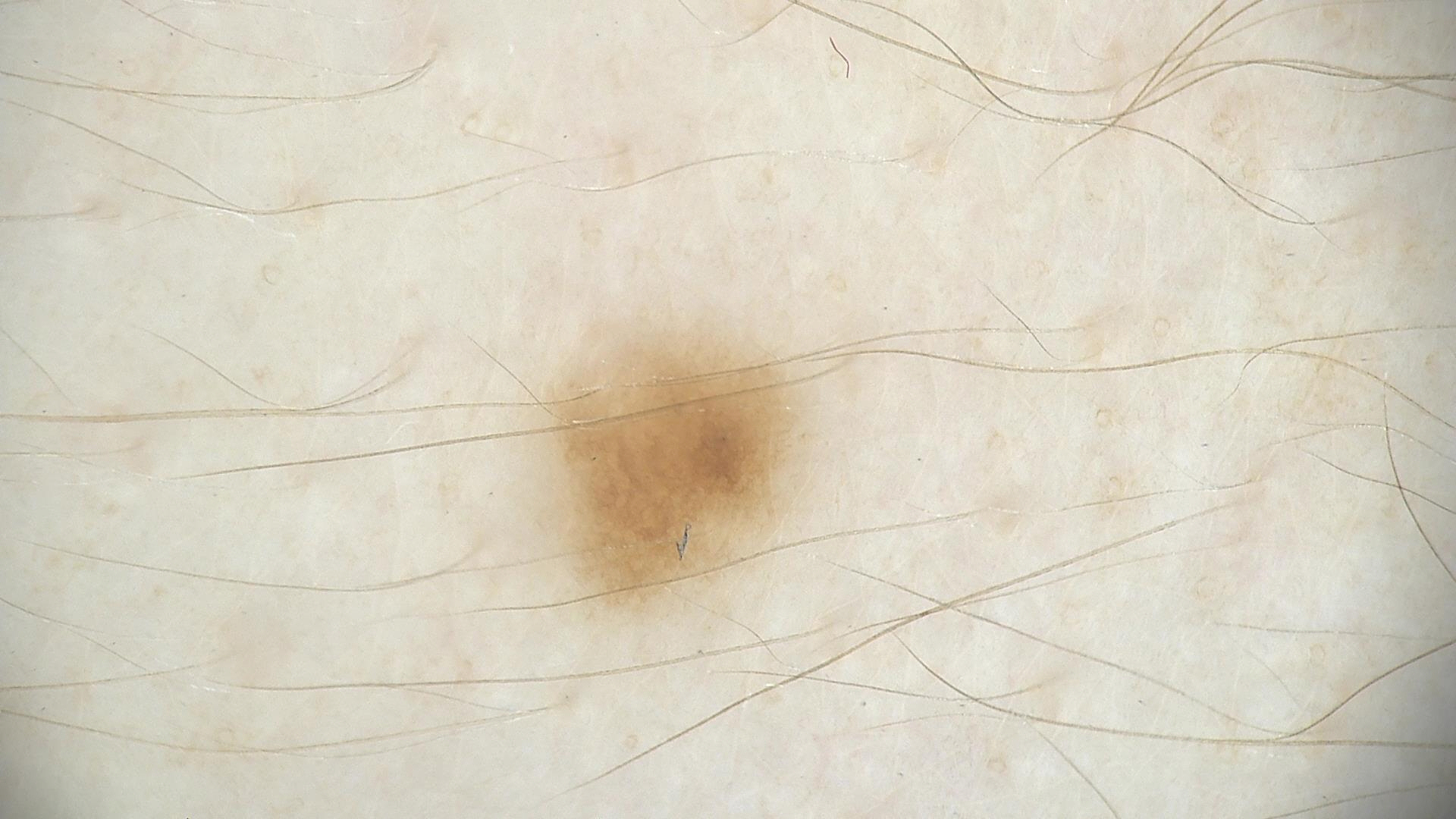The diagnosis was a dysplastic junctional nevus.